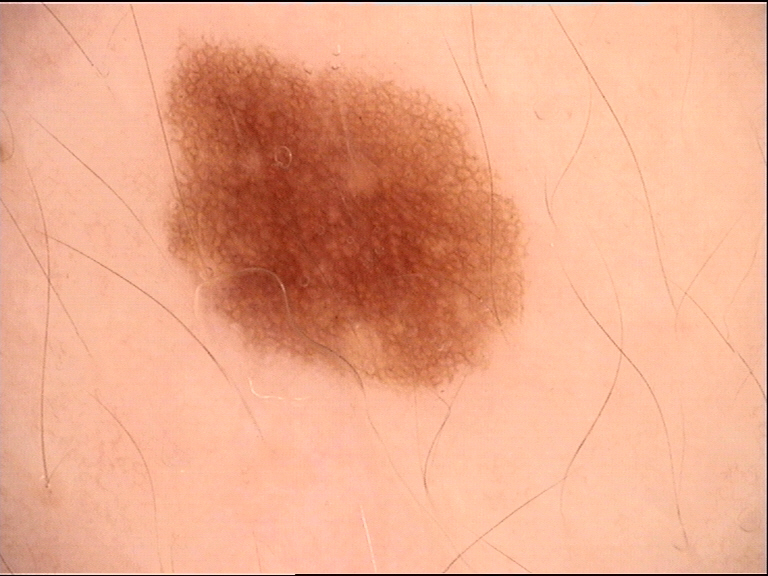Q: What was the diagnostic impression?
A: dysplastic junctional nevus (expert consensus)